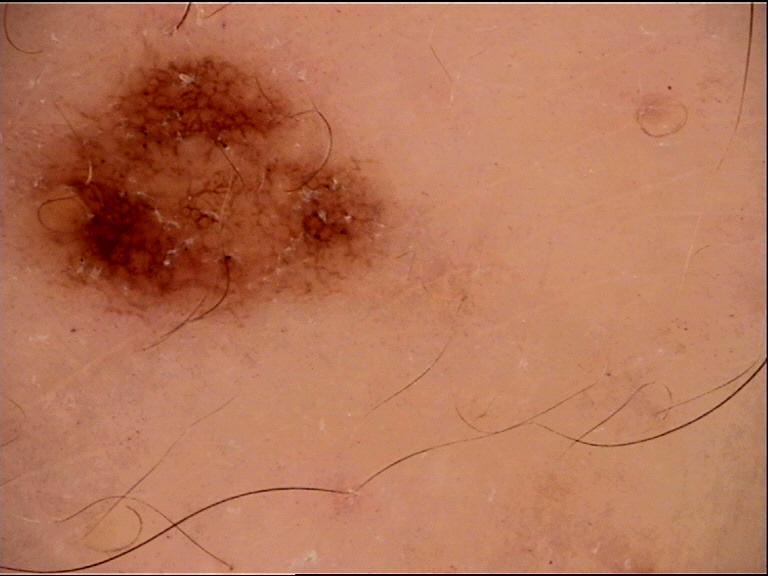Classified as a dysplastic compound nevus.